A skin lesion imaged with a dermatoscope.
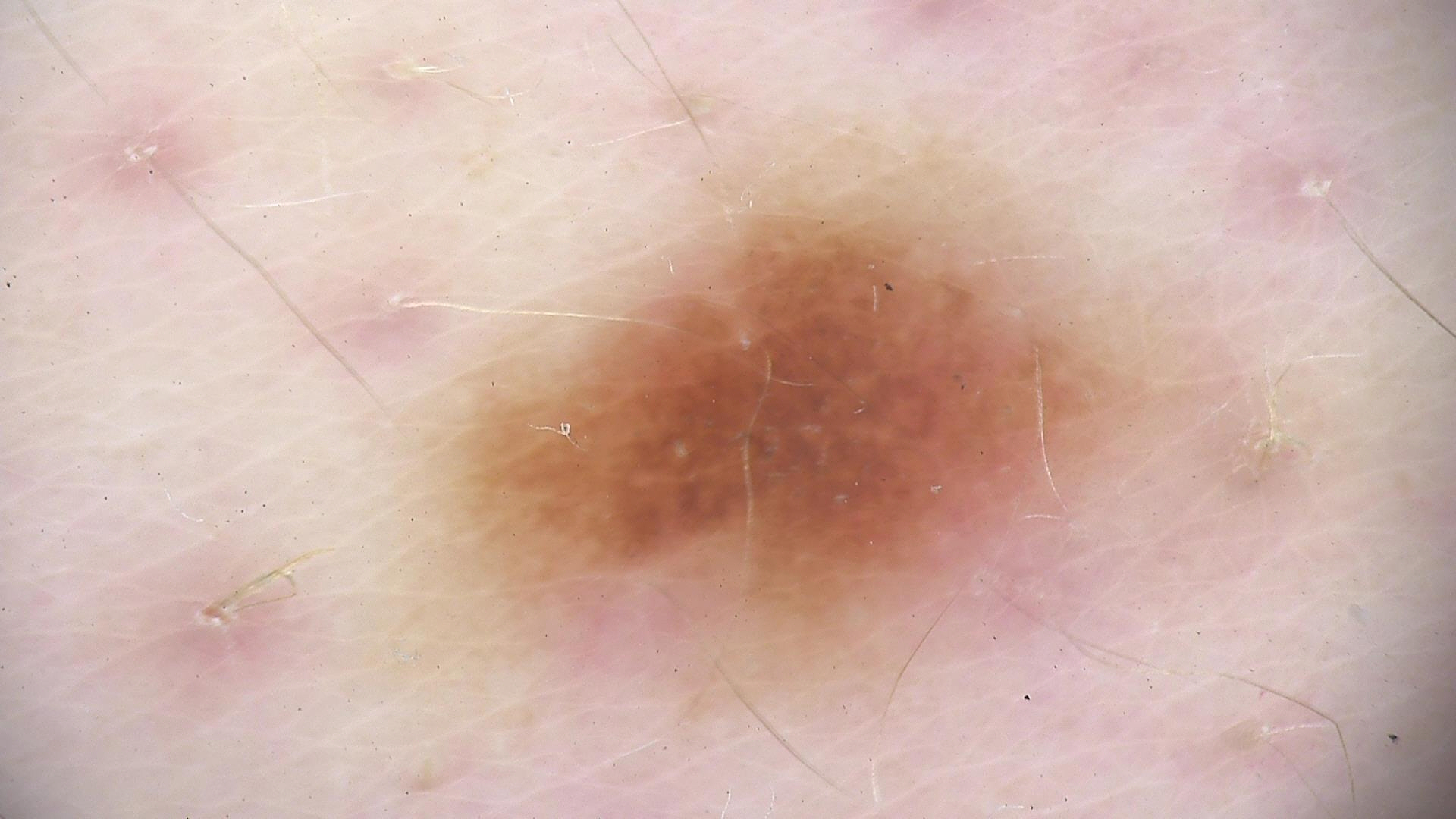Case:
– assessment · dysplastic junctional nevus (expert consensus)